A close-up photograph; the patient did not report lesion symptoms; the contributor is 40–49, female; the lesion is described as fluid-filled and raised or bumpy; present for less than one week; the arm is involved:
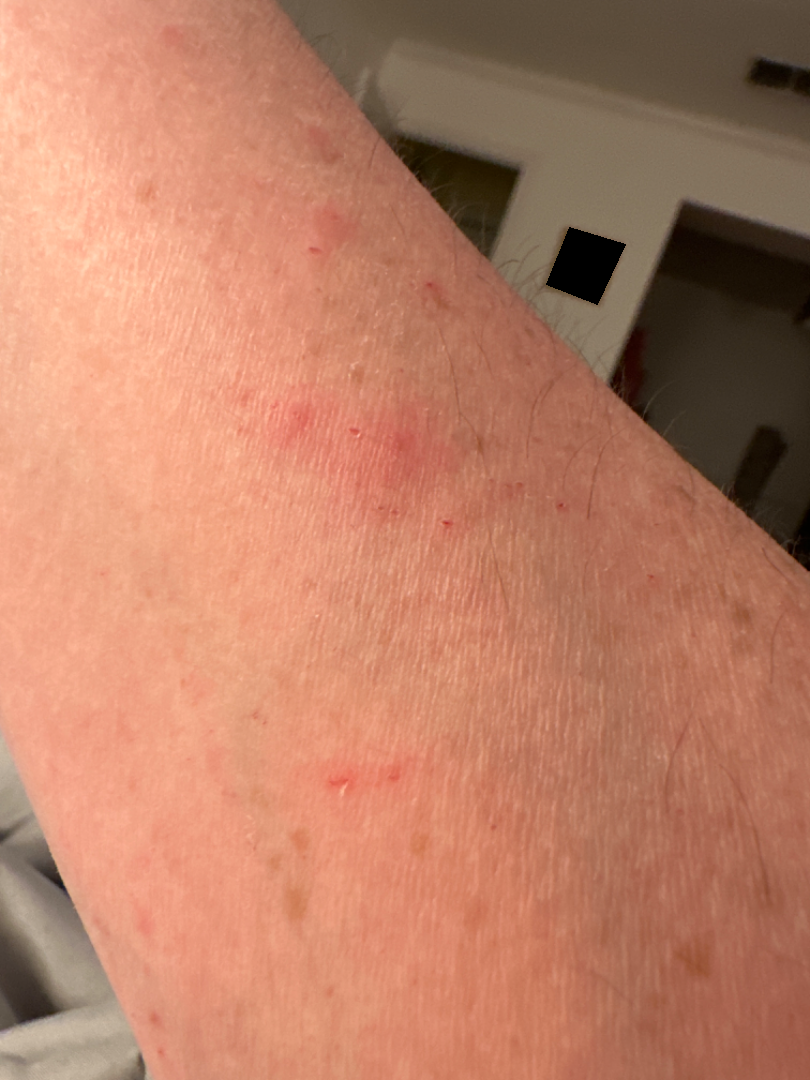<case>
  <differential>
    <tied_lead>Insect Bite, Eczema, Allergic Contact Dermatitis</tied_lead>
  </differential>
</case>